By self-report, no personal history of skin cancer; the patient describes having few moles overall; a female subject age 39; the patient says their skin reddens with sun exposure; a dermoscopy image of a skin lesion.
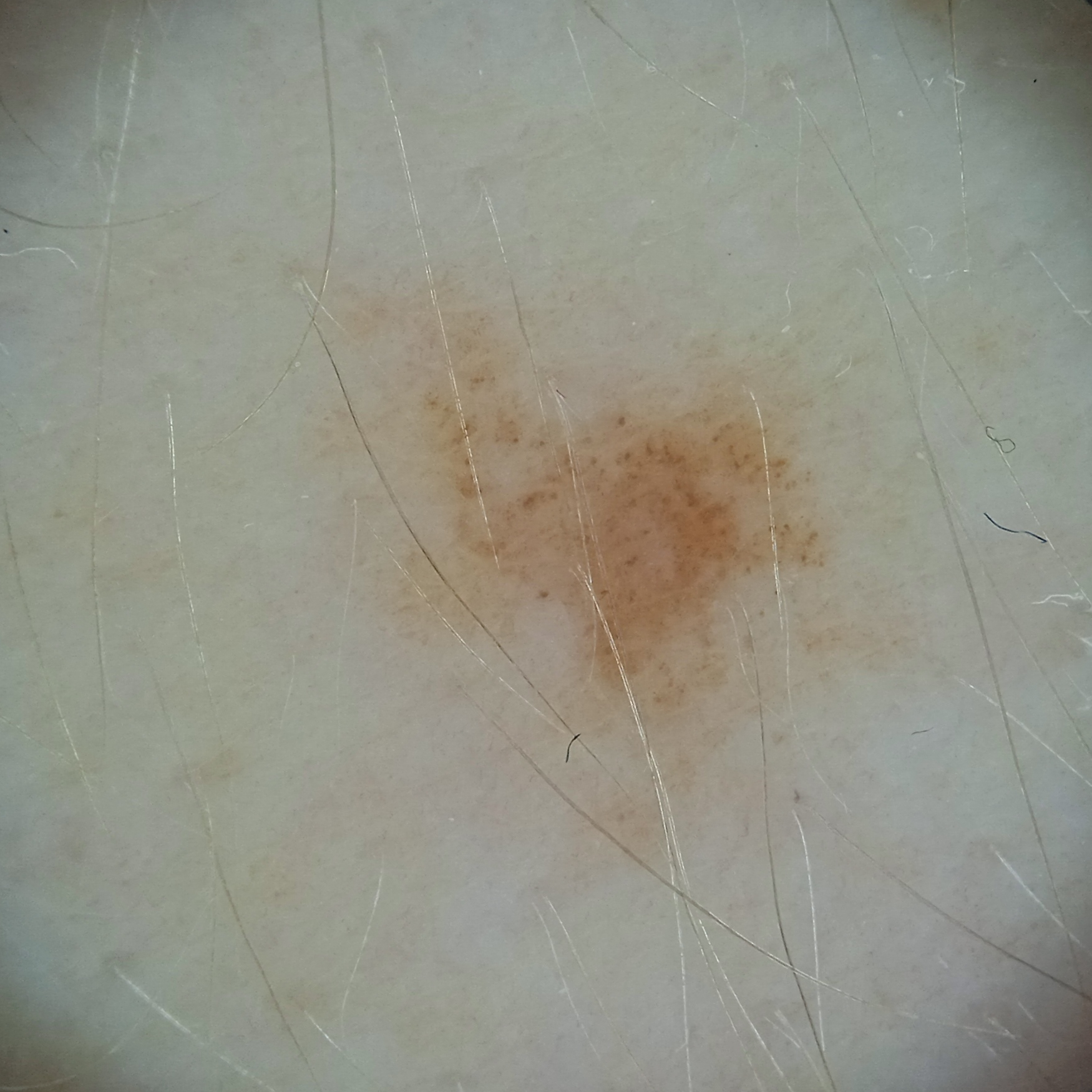<record>
  <lesion_location>an arm</lesion_location>
  <lesion_size>
    <diameter_mm>5.1</diameter_mm>
  </lesion_size>
  <diagnosis>
    <name>melanocytic nevus</name>
    <malignancy>benign</malignancy>
  </diagnosis>
</record>